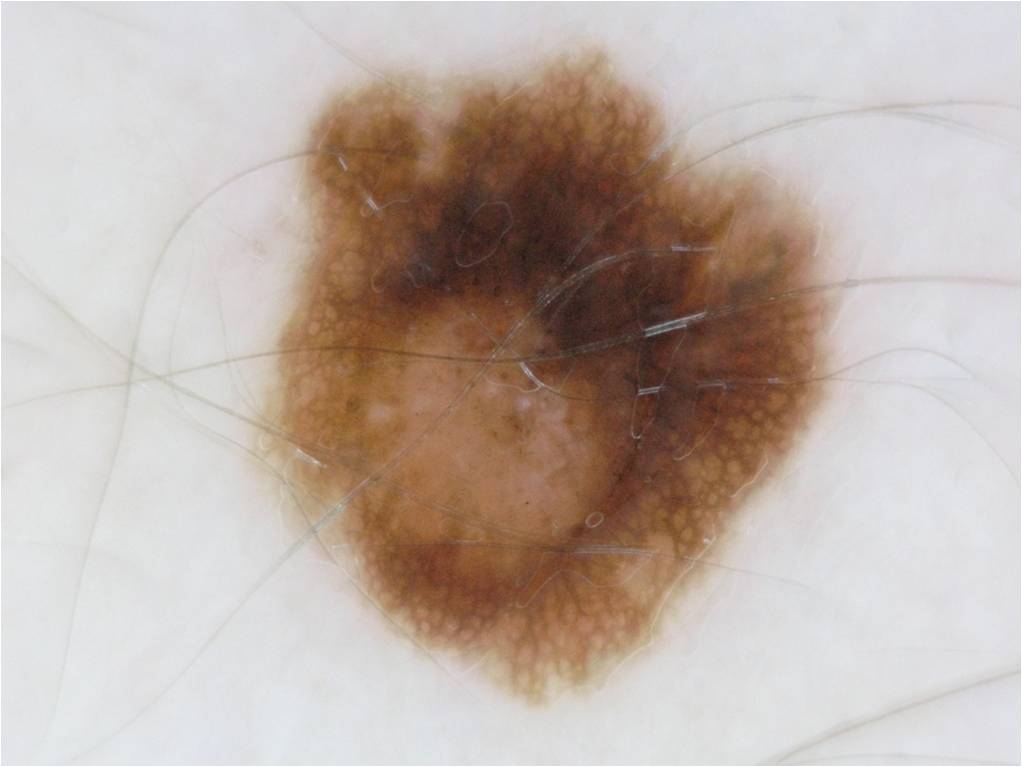imaging: dermoscopy of a skin lesion; lesion bbox: 263/51/835/693; impression: a melanocytic nevus.